The patient described the issue as a rash. The lesion is associated with pain, itching and burning. The patient notes the condition has been present for less than one week. The lesion involves the head or neck. Texture is reported as rough or flaky. This image was taken at a distance: 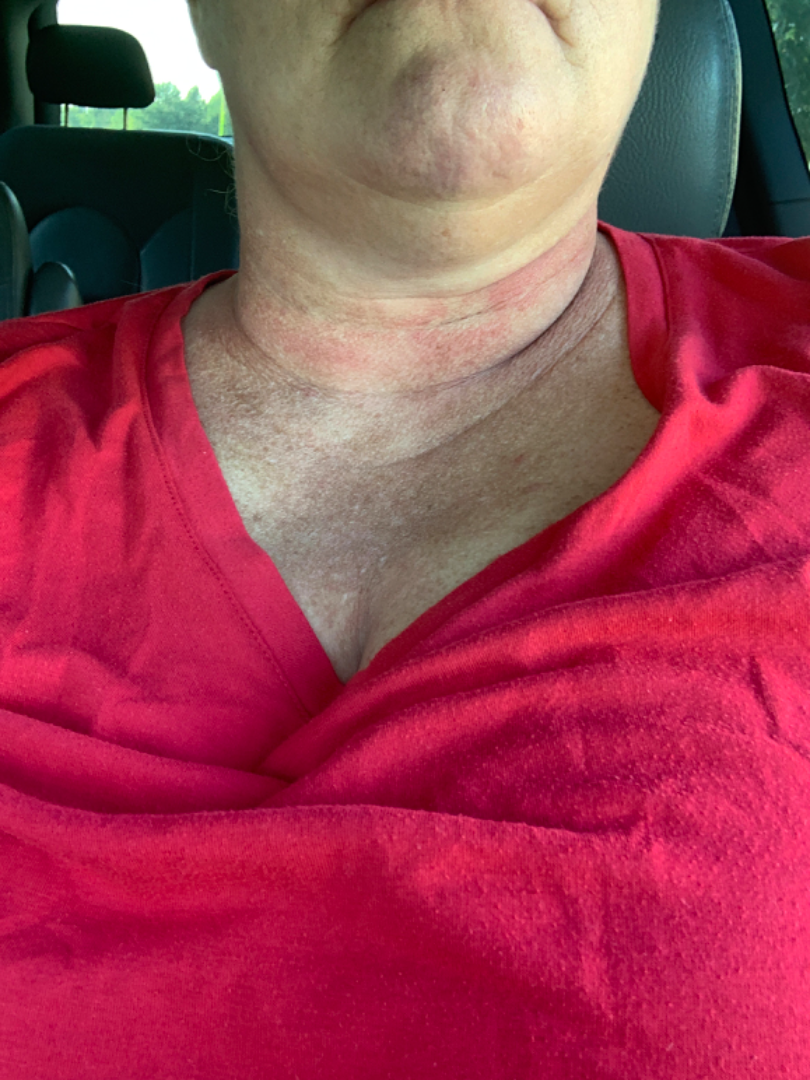Q: What is the differential diagnosis?
A: a single dermatologist reviewed the case: the differential includes Photocontact dermatitis [berloque dermatitis], Allergic Contact Dermatitis and Irritant Contact Dermatitis, with no clear leading consideration